Dermoscopy of a skin lesion:
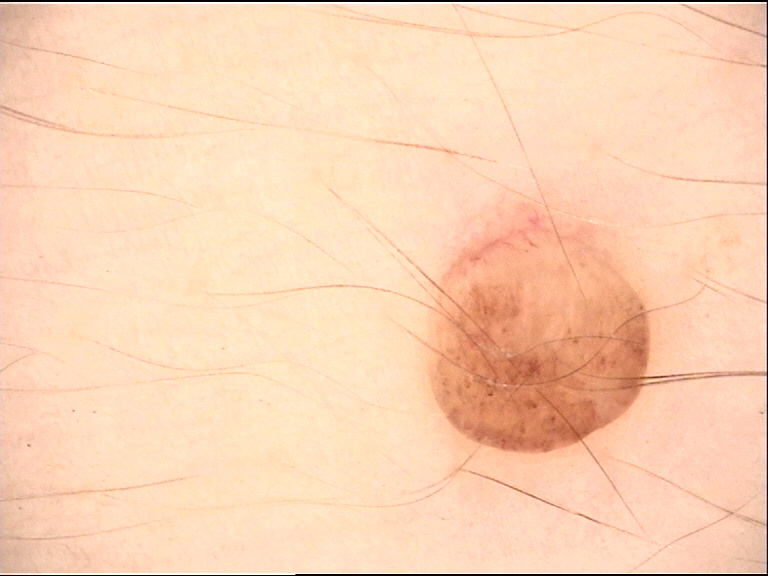assessment: dermal nevus (expert consensus)